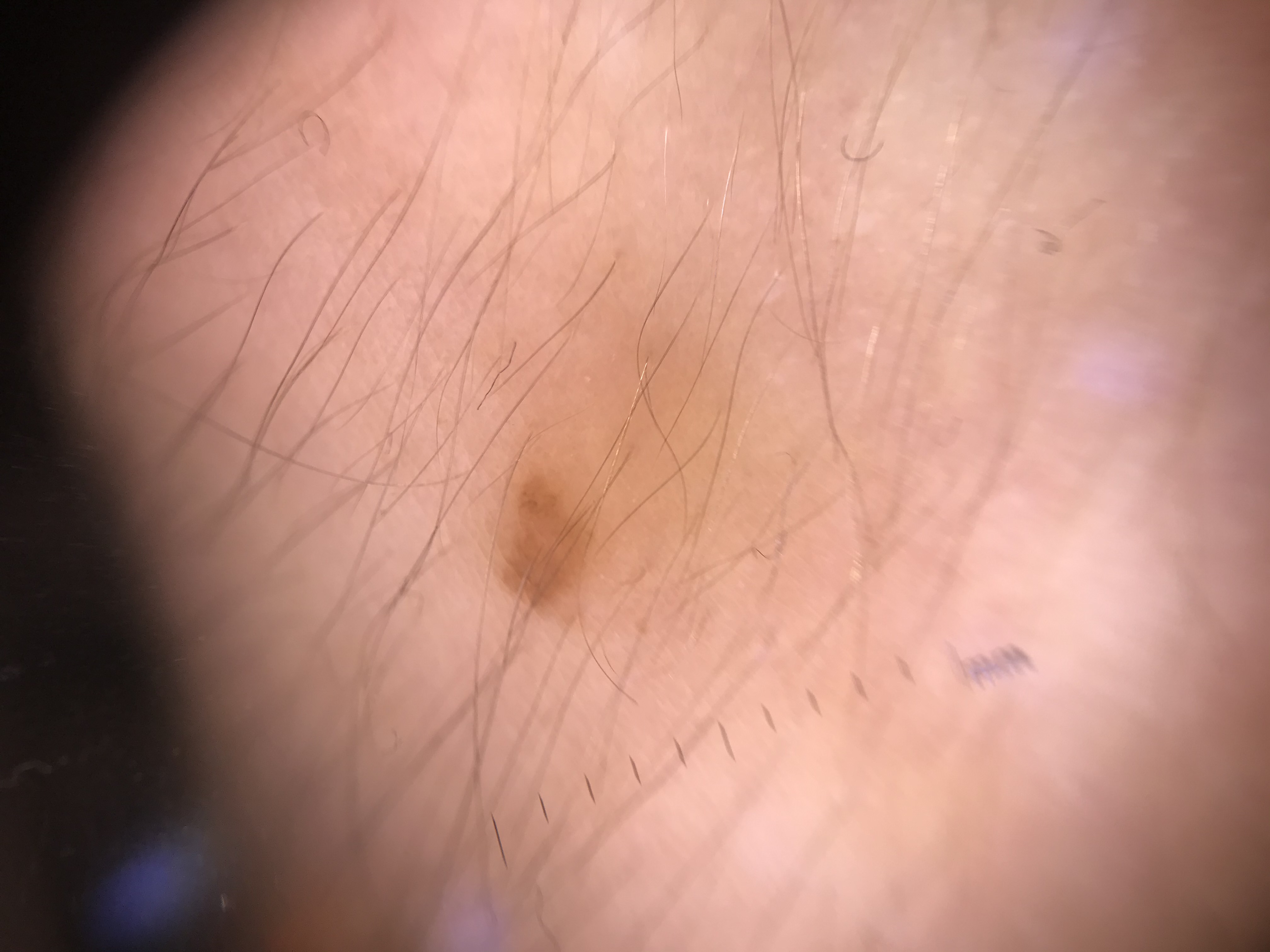| feature | finding |
|---|---|
| label | junctional nevus (expert consensus) |